A dermatoscopic image of a skin lesion: 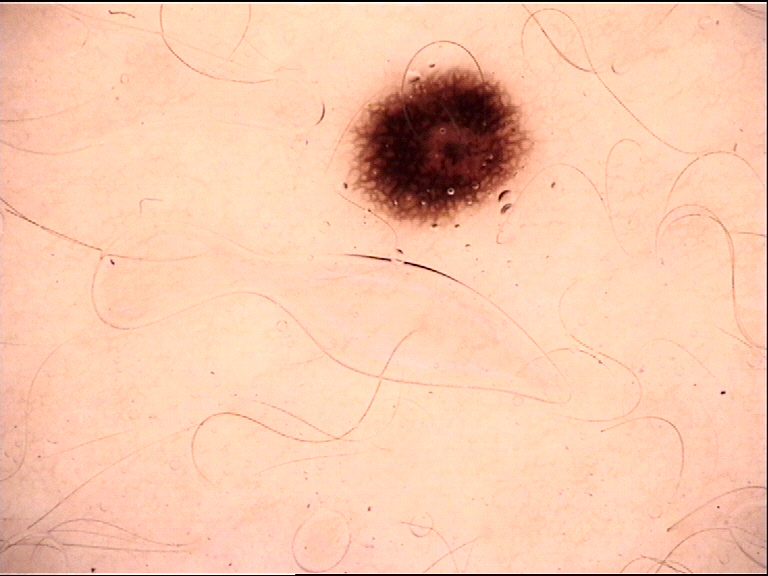{
  "diagnosis": {
    "name": "dysplastic junctional nevus",
    "code": "jd",
    "malignancy": "benign",
    "super_class": "melanocytic",
    "confirmation": "expert consensus"
  }
}